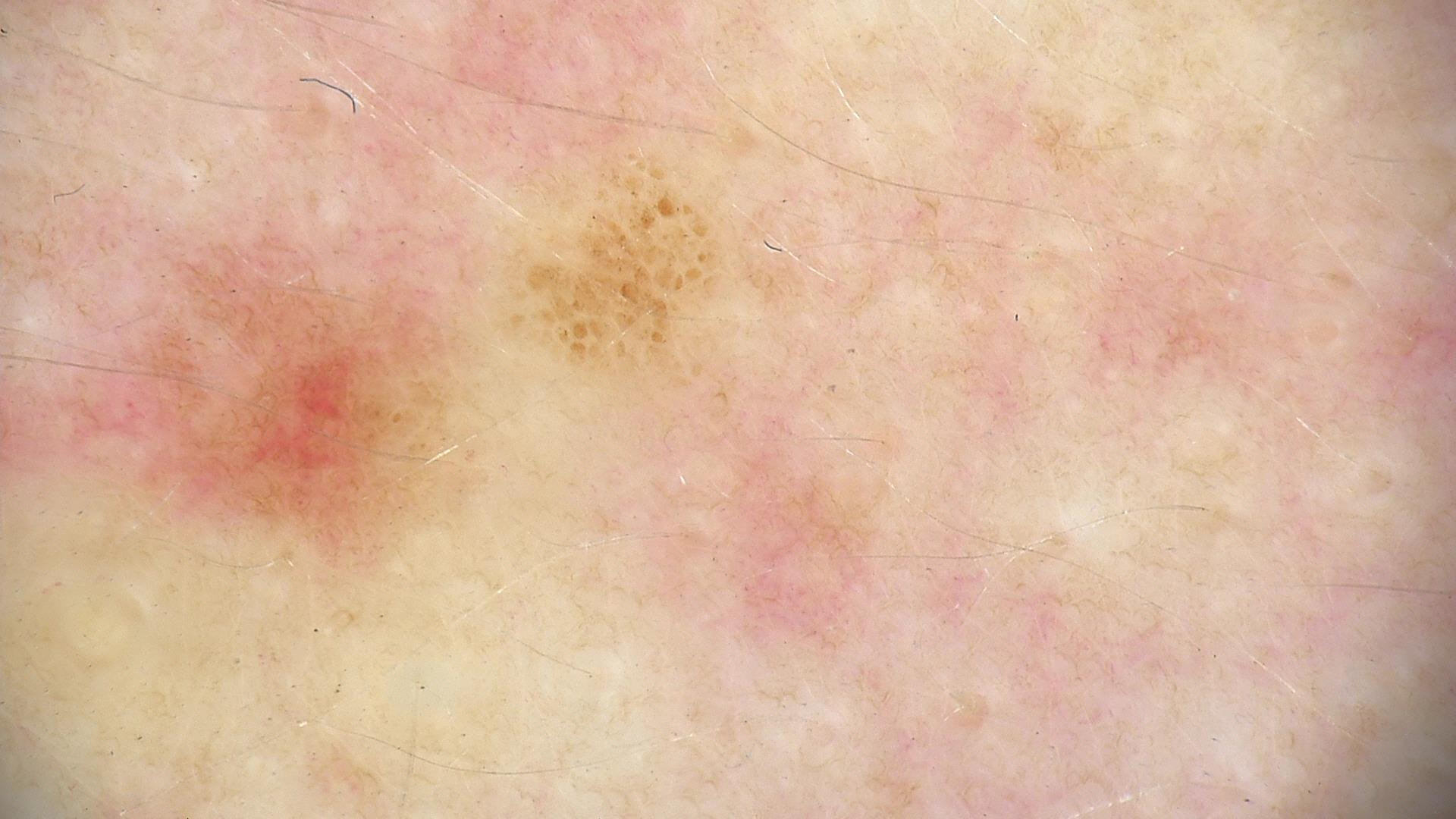A dermoscopic close-up of a skin lesion. This is a banal lesion. Consistent with a junctional nevus.